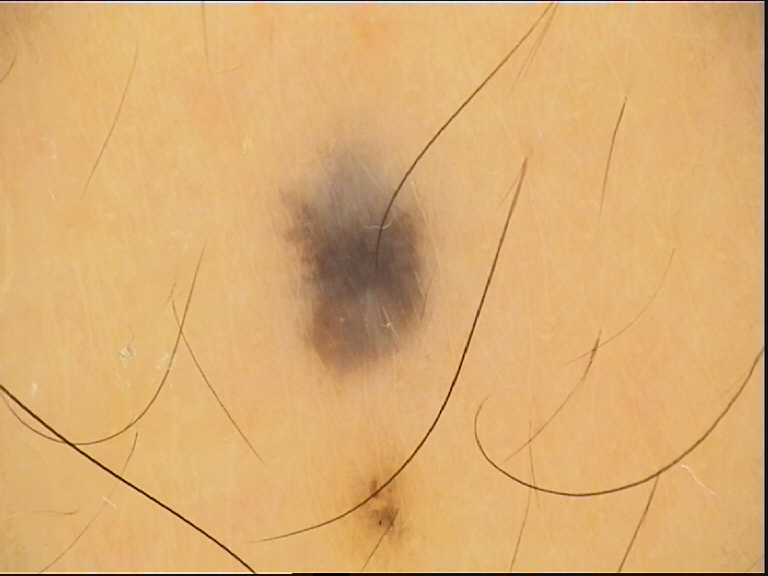Q: What kind of image is this?
A: dermoscopy
Q: What was the diagnostic impression?
A: blue nevus (expert consensus)